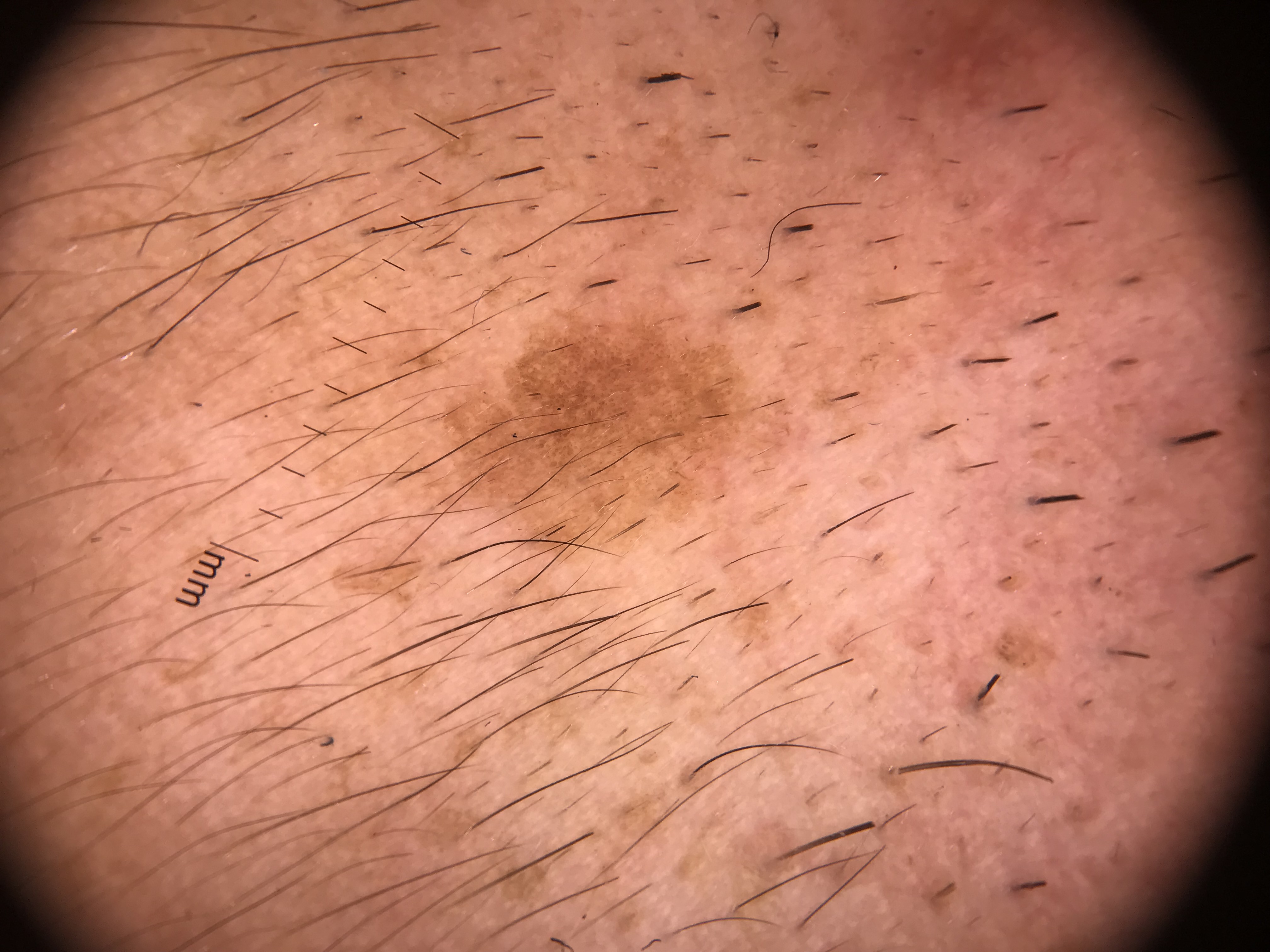Labeled as a junctional nevus.